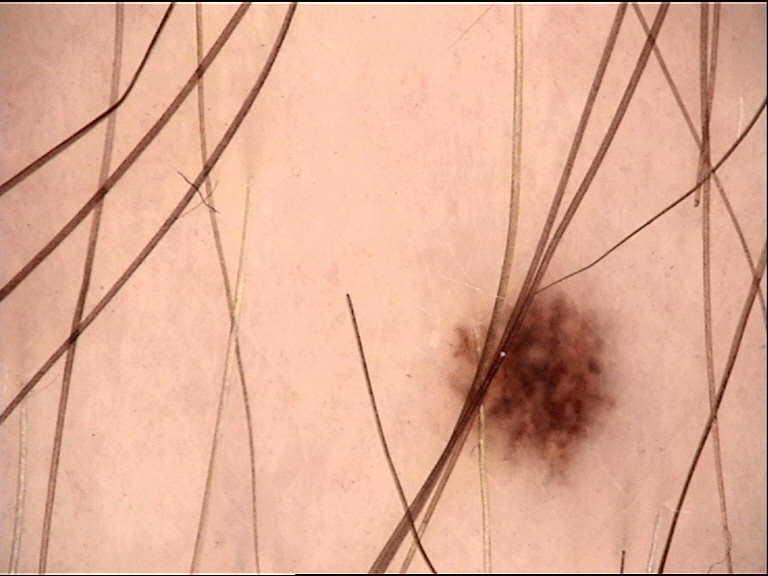Q: What was the diagnostic impression?
A: dysplastic junctional nevus (expert consensus)